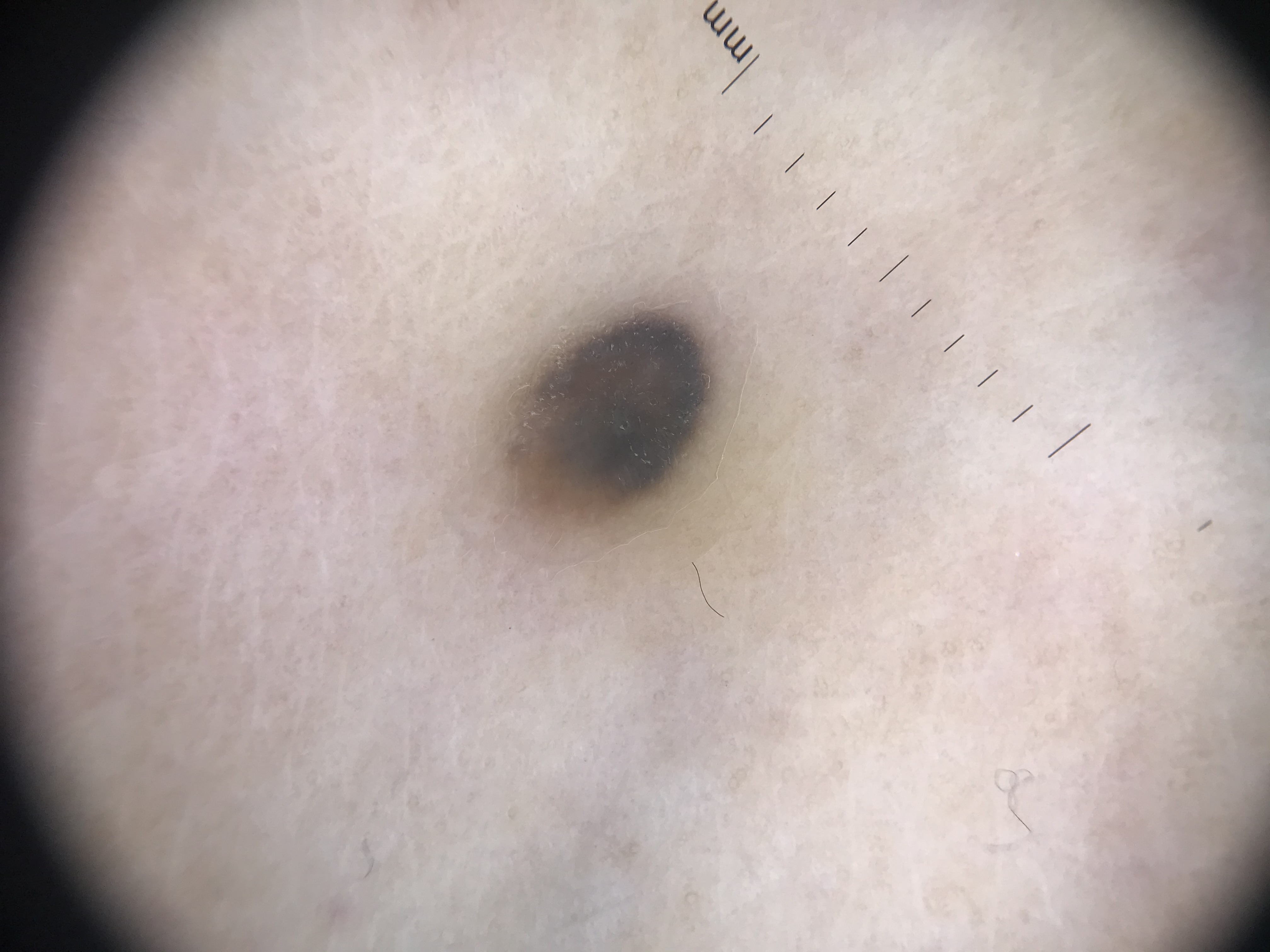Conclusion:
The diagnosis was a blue nevus.